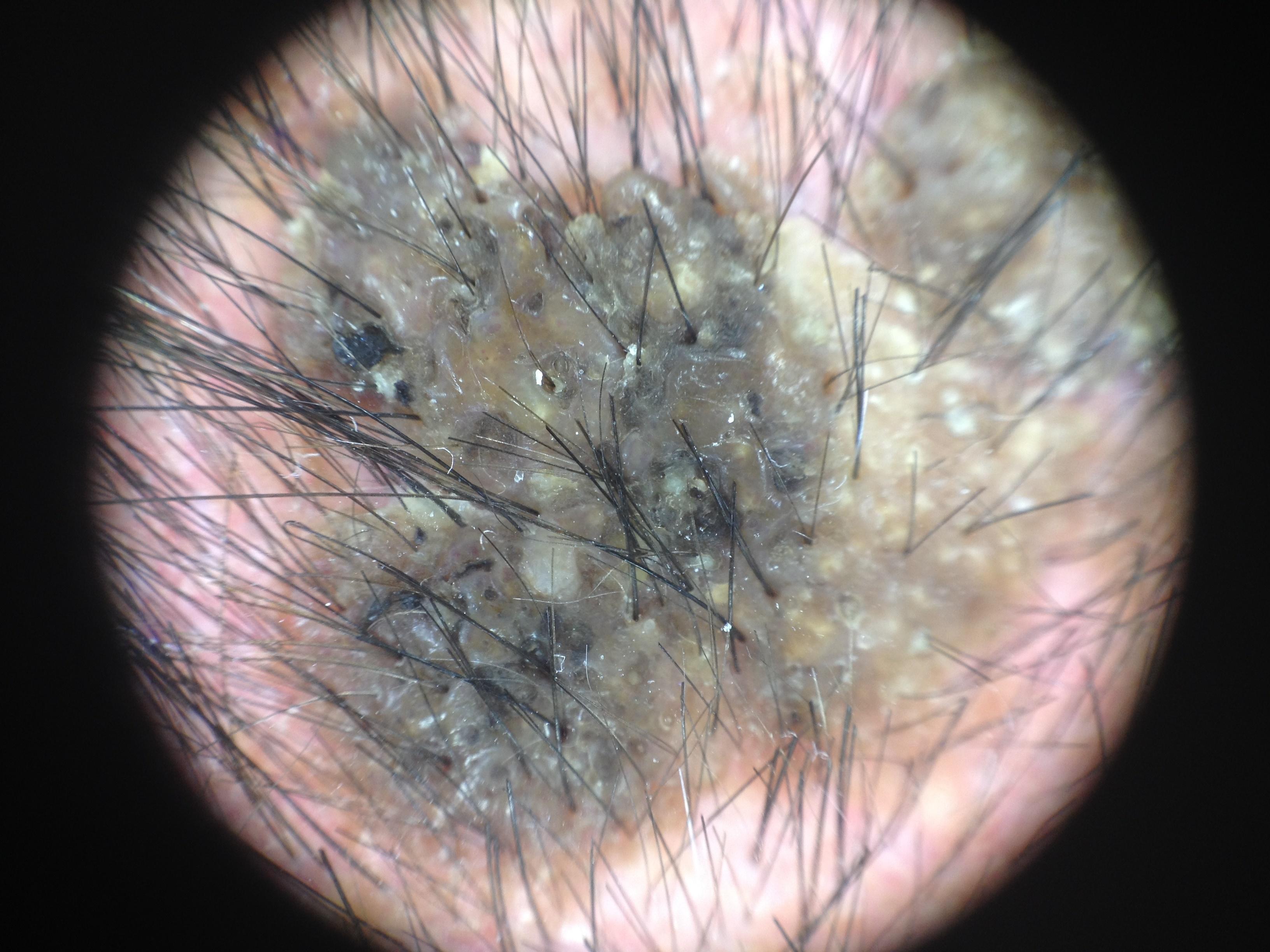{"image": "dermatoscopic image", "lesion_location": {"region": "the head or neck"}, "diagnosis": {"name": "Seborrheic keratosis", "malignancy": "benign", "confirmation": "expert clinical impression", "lineage": "epidermal"}}